The photograph is a close-up of the affected area · no associated systemic symptoms reported · present for one to three months.
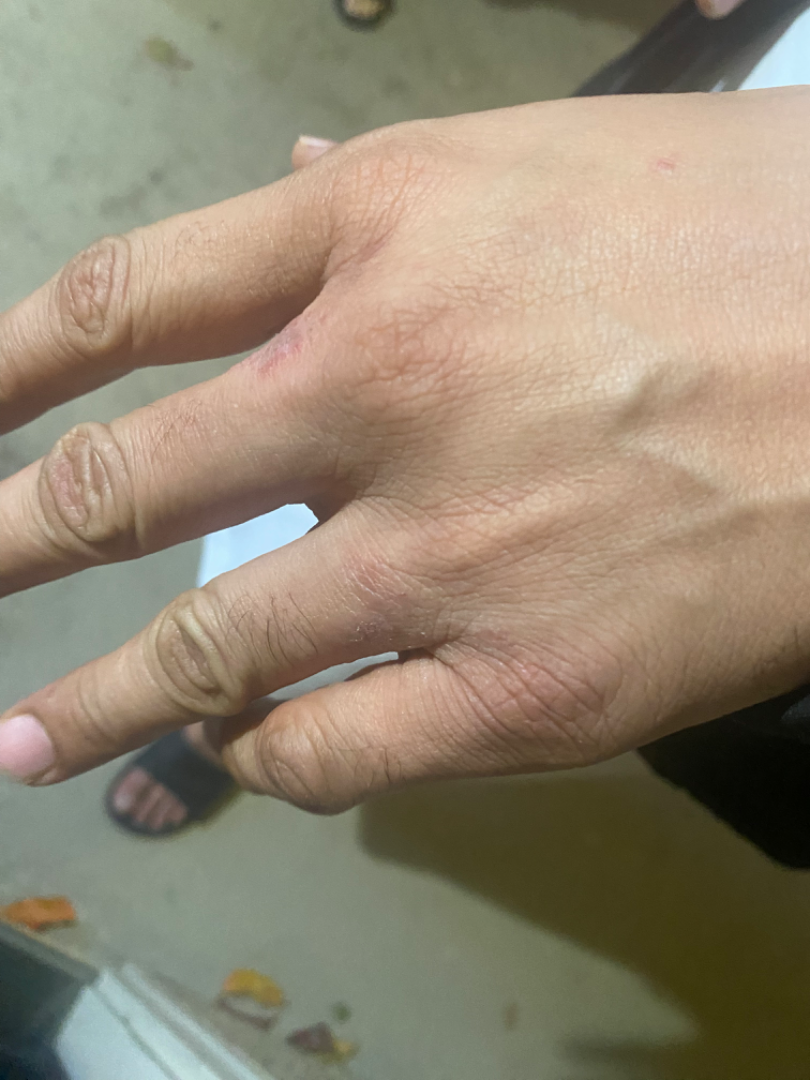Findings:
* assessment · unable to determine